A macroscopic clinical photograph of a skin lesion. The patient describes having few moles overall. The patient says their skin tans without first burning. The patient reports a personal history of cancer:
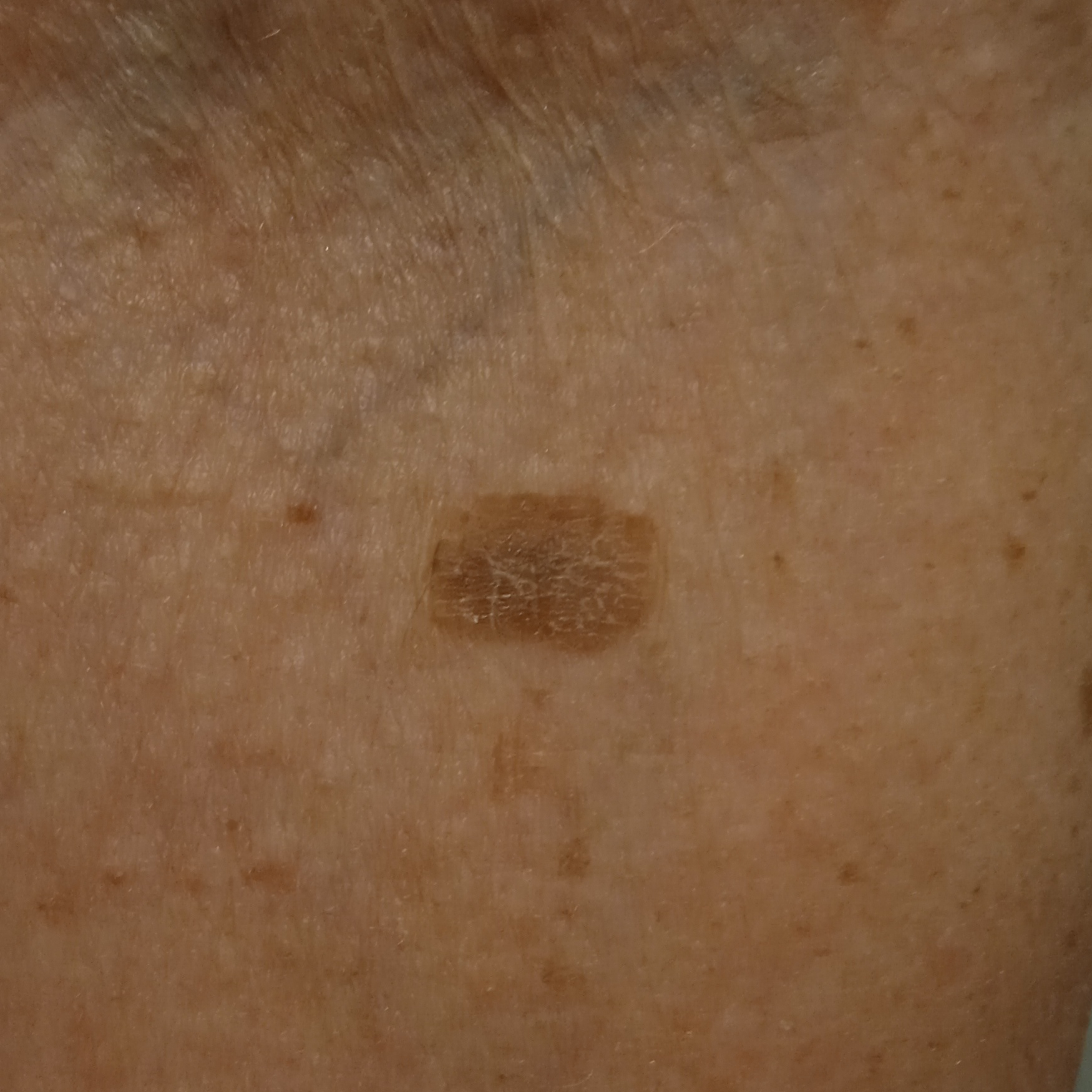Case:
– site: an arm
– size: 11.2 mm
– assessment: seborrheic keratosis (dermatologist consensus)